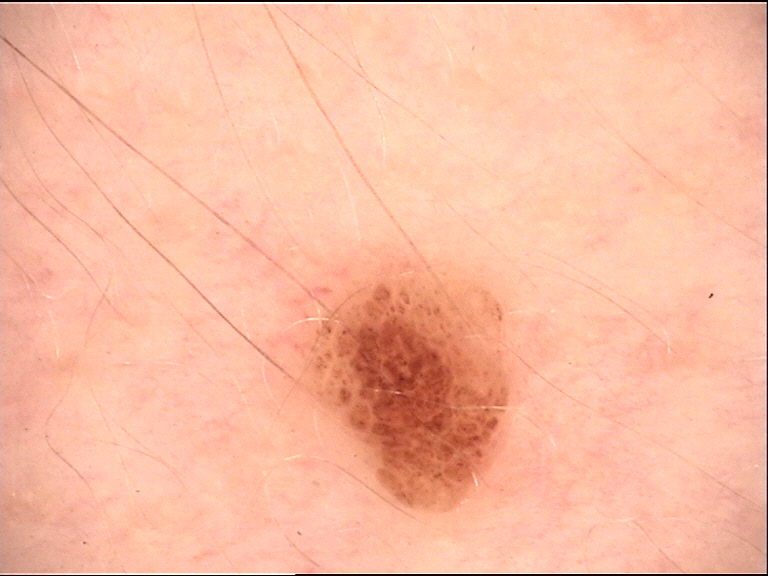A dermoscopic close-up of a skin lesion.
Labeled as a compound nevus.